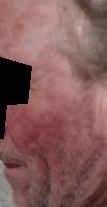Patient information:
Skin tone: Fitzpatrick phototype I; human graders estimated MST 1 or 2 (two reviewer pools). The condition has been present for three to twelve months. Located on the front of the torso and head or neck. The patient reports associated shortness of breath and fatigue. The patient reports enlargement, bothersome appearance and itching. The patient is a male aged 50–59. An image taken at a distance.
Review:
Most consistent with Seborrheic Dermatitis.